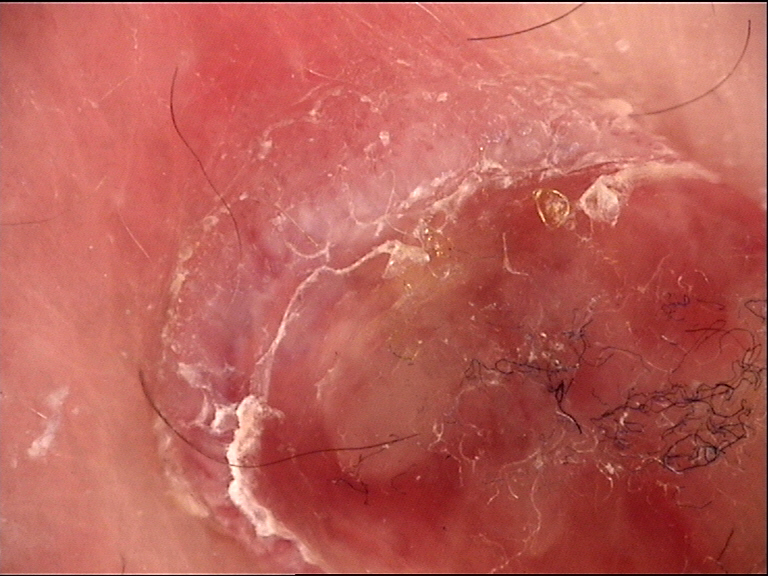Histopathology confirmed a Kaposi sarcoma.